A dermoscopic close-up of a skin lesion — 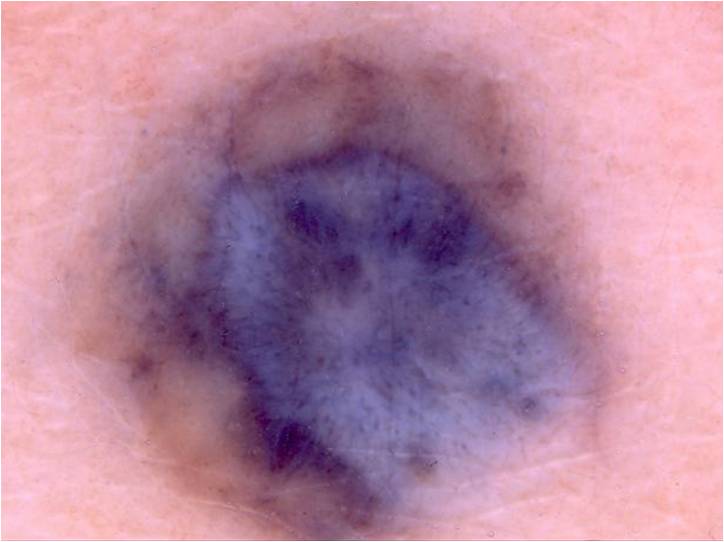dermoscopic features assessed but absent: globules, pigment network, negative network, milia-like cysts, and streaks
lesion bbox: 57, 13, 647, 539
diagnostic label: a melanocytic nevus, a benign lesion